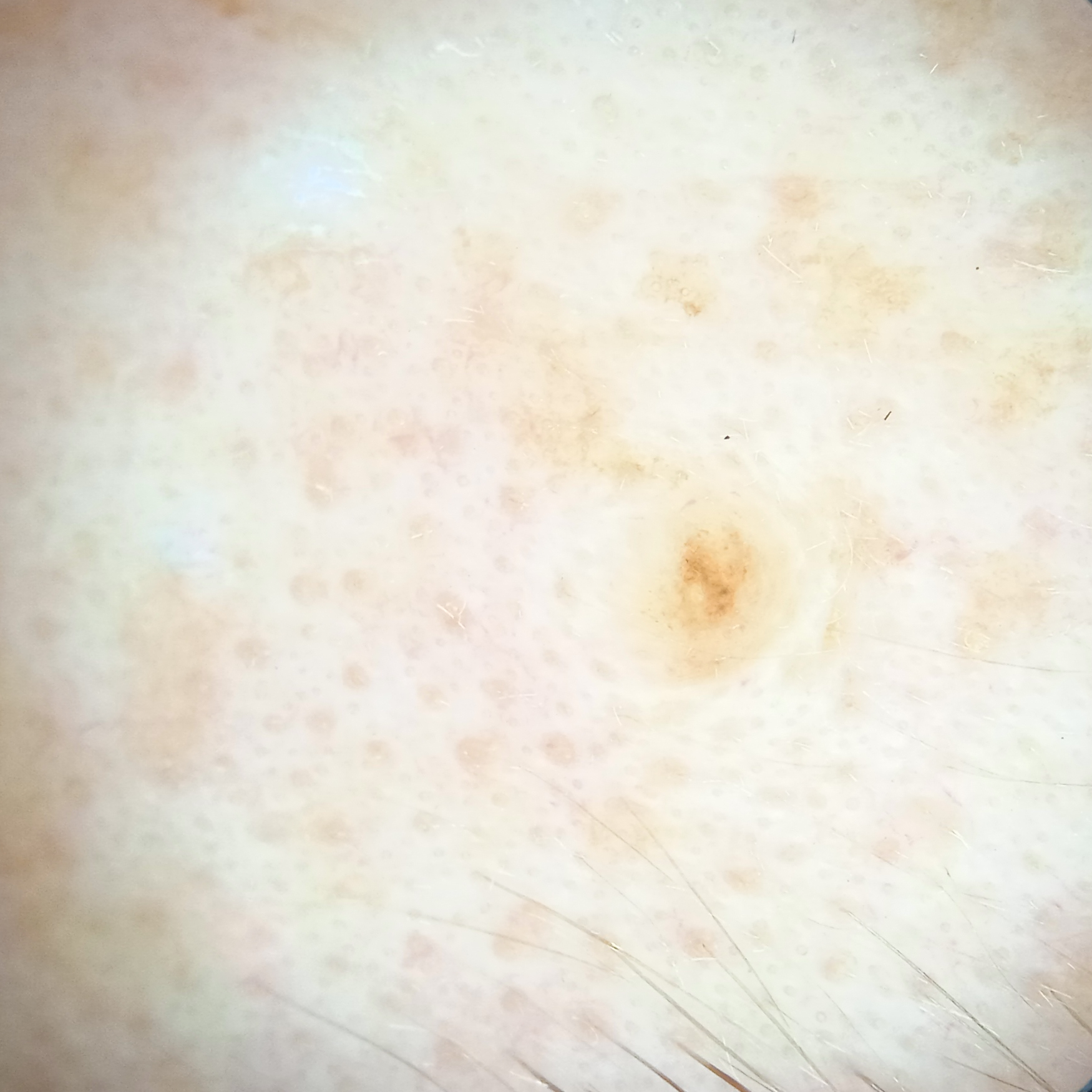nevus count = a moderate number of melanocytic nevi | sun reaction = skin reddens painfully with sun exposure | image type = dermoscopic image | referral context = clinical suspicion of melanoma | subject = female, 50 years of age | anatomic site = the face | size = 1.8 mm | diagnosis = melanocytic nevus (dermatologist consensus).